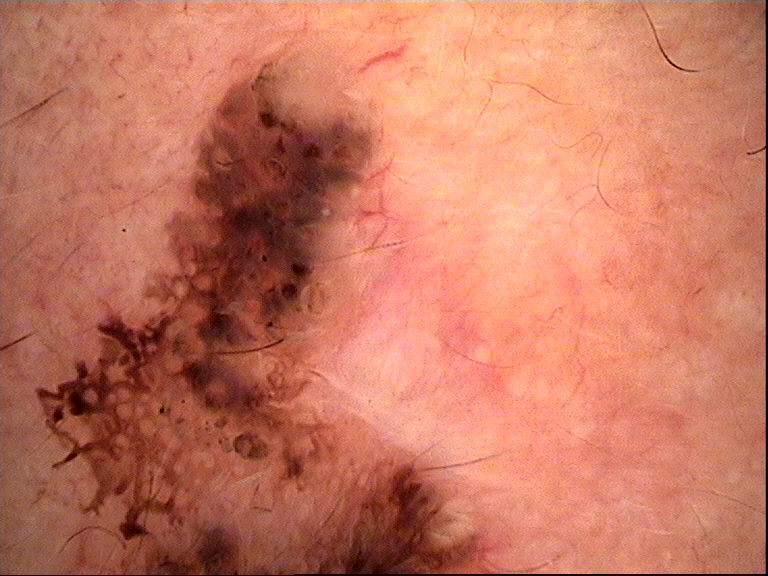{"image": "dermoscopy", "lesion_type": {"main_class": "keratinocytic"}, "diagnosis": {"name": "seborrheic keratosis", "code": "sk", "malignancy": "benign", "super_class": "non-melanocytic", "confirmation": "expert consensus"}}